A clinical photograph showing a skin lesion · a patient 72 years old.
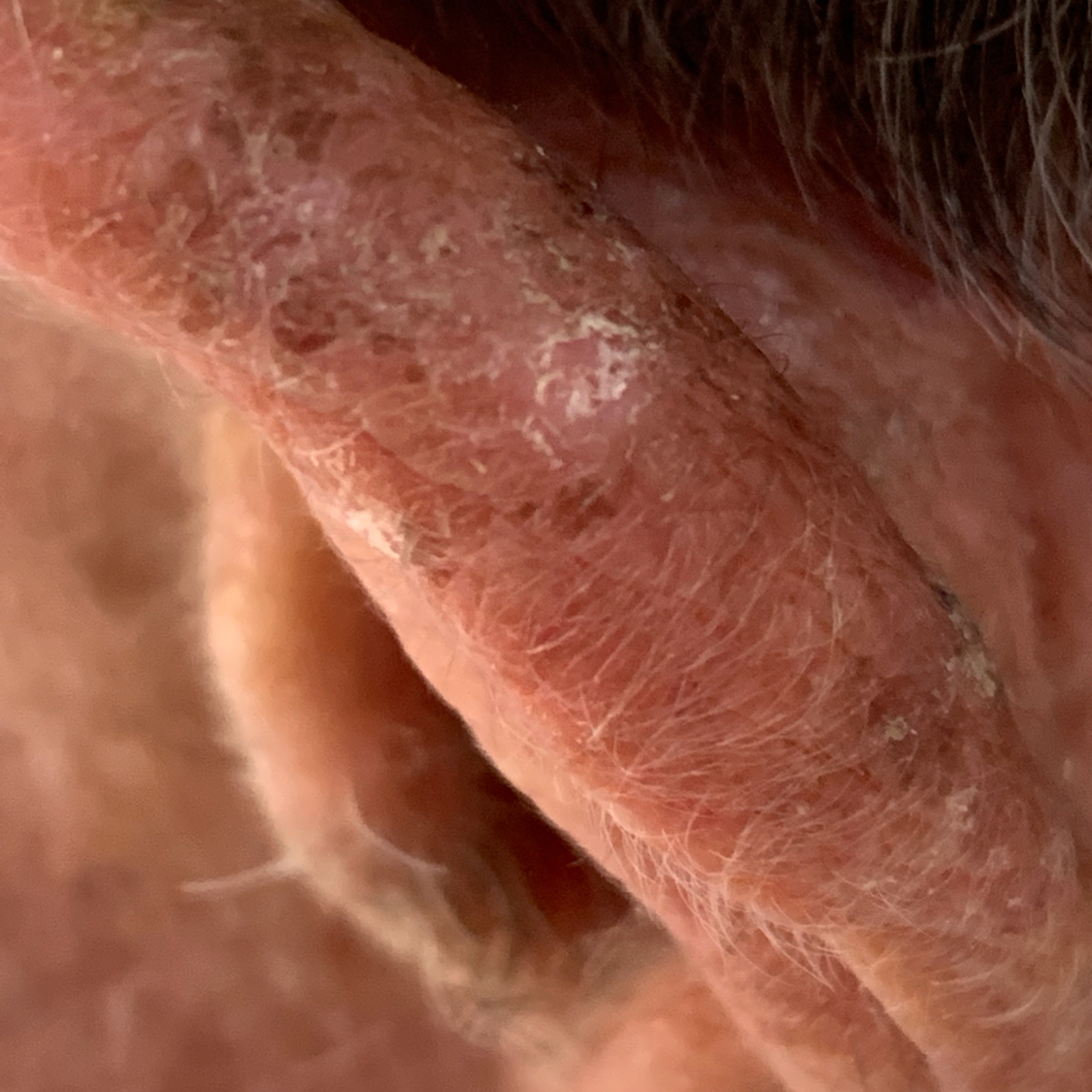Clinical context: The lesion was found on an ear. Conclusion: The diagnostic impression was an actinic keratosis.